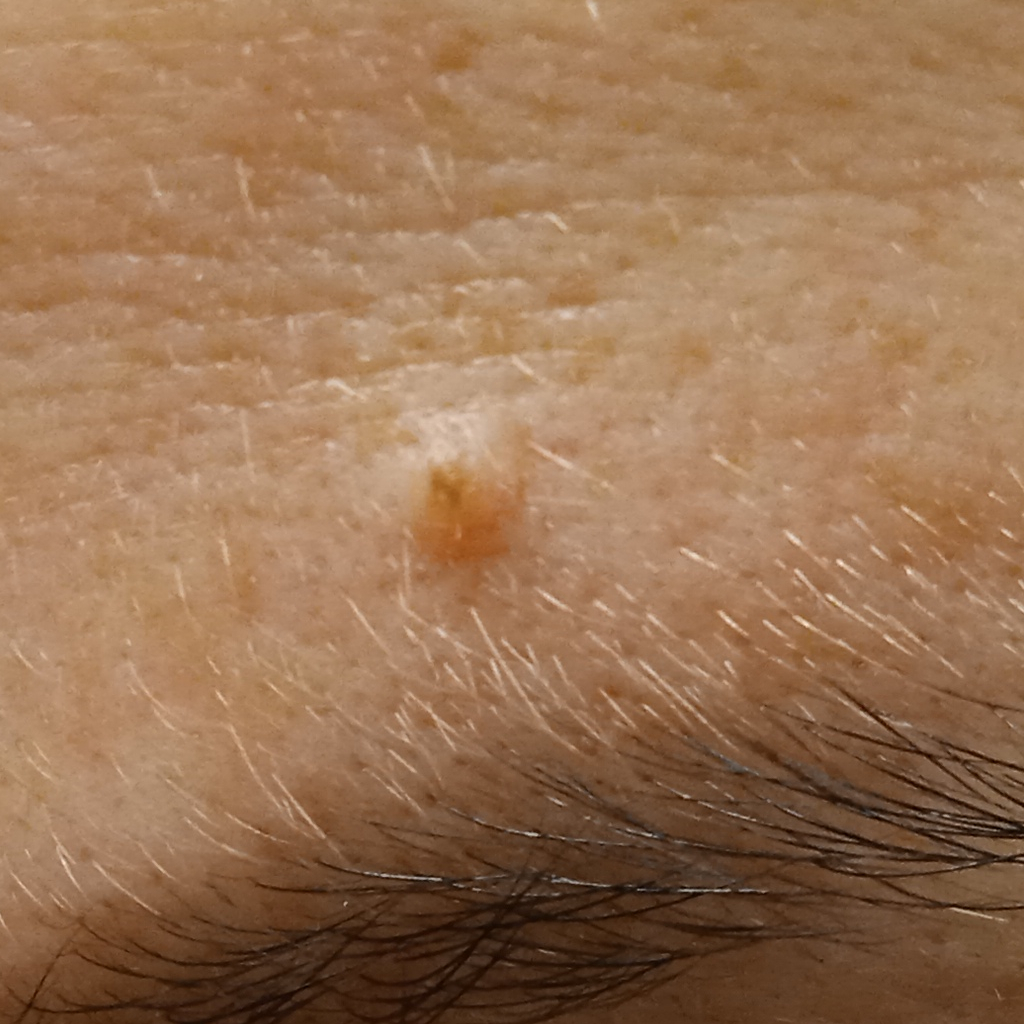Clinical context: A female subject age 50. A moderate number of moles by the patient's own estimate. The referring clinician suspected melanoma. The patient says their skin reddens painfully with sun exposure. A clinical photograph showing a skin lesion. The lesion is located on the face. The lesion is about 1.8 mm across. Impression: The lesion was assessed as a melanocytic nevus.